A dermoscopic close-up of a skin lesion:
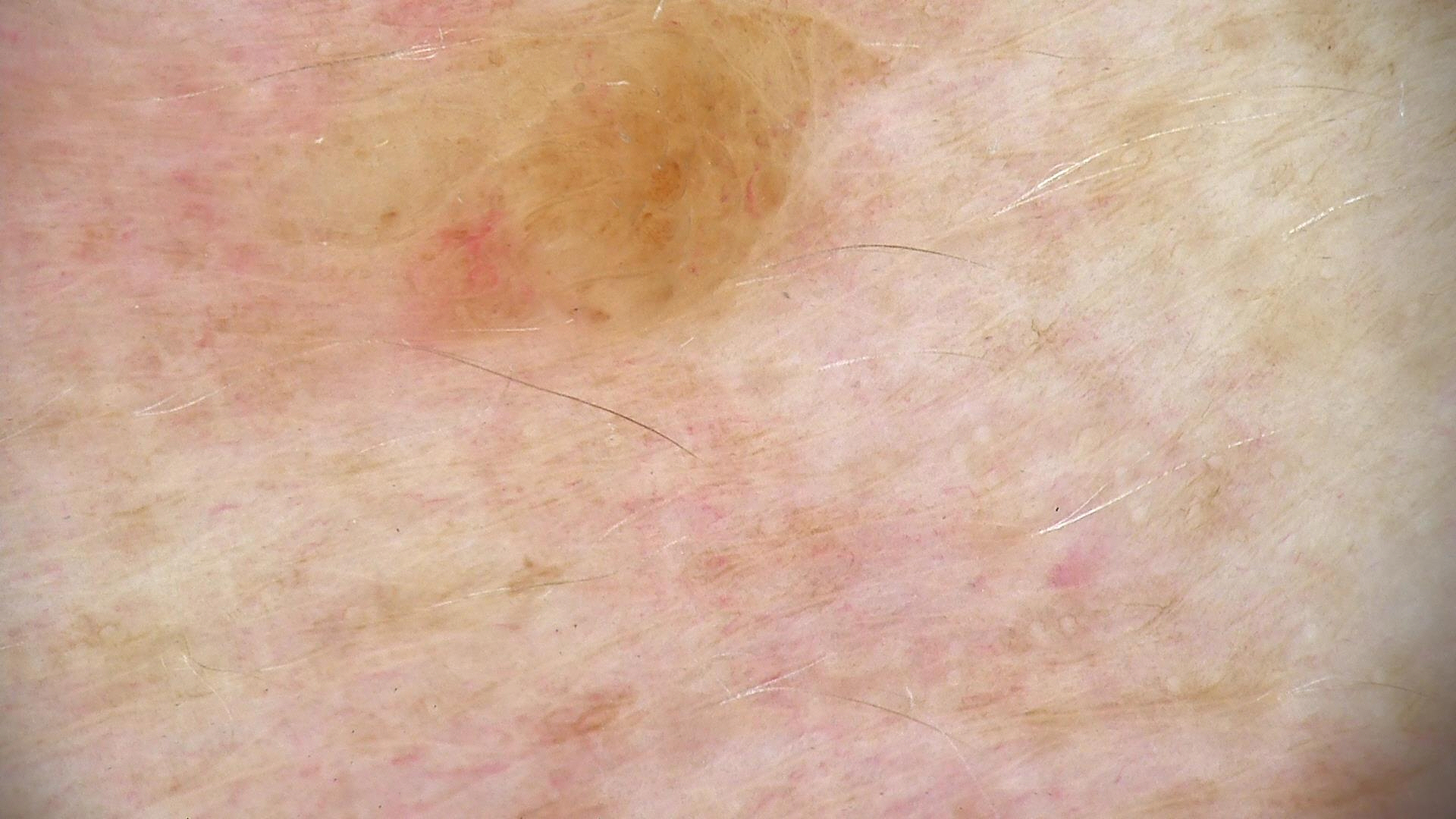Classified as a dermal nevus.